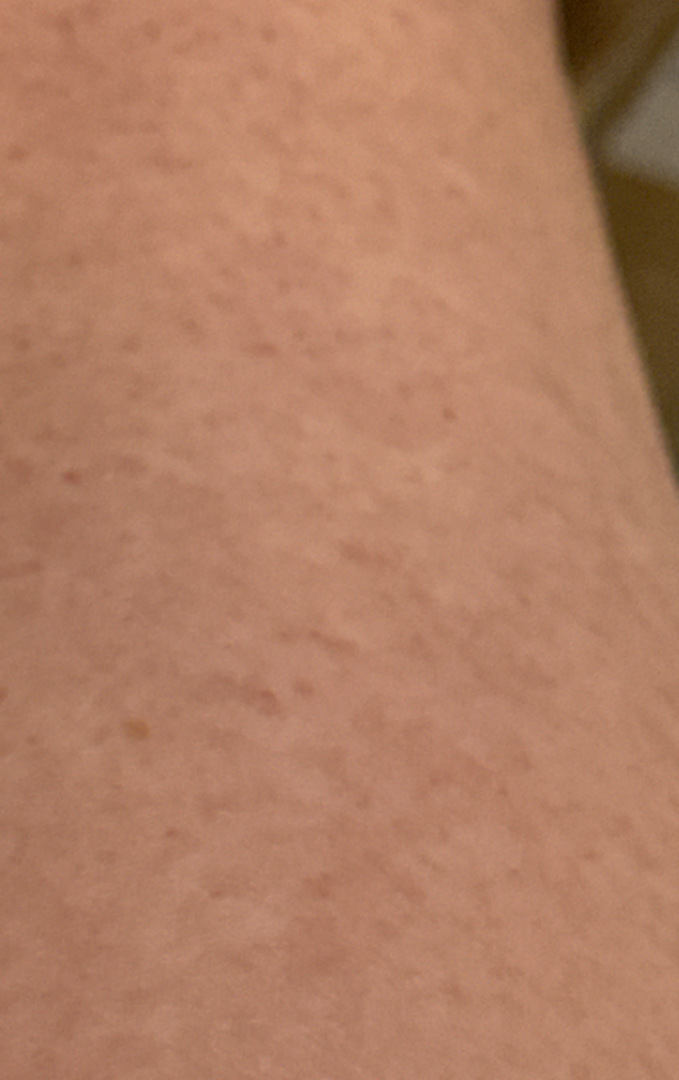The case was indeterminate on photographic review.